A dermoscopy image of a single skin lesion.
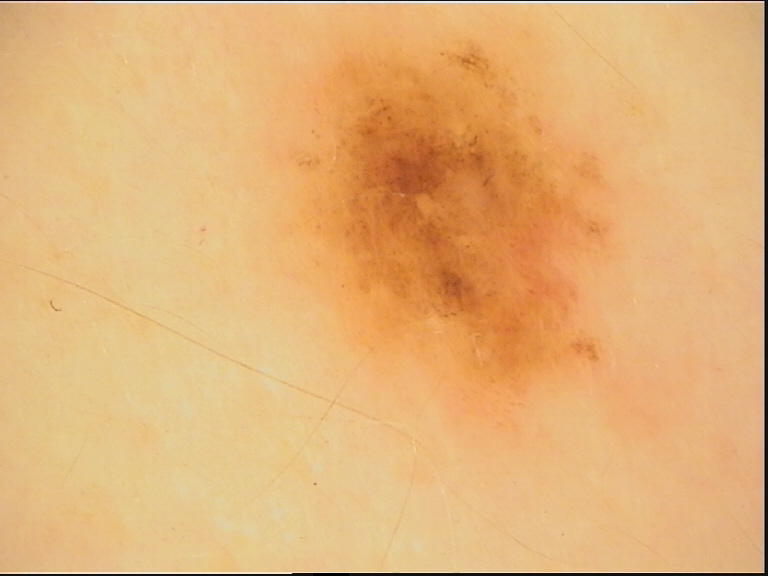– diagnosis: dysplastic junctional nevus (expert consensus)